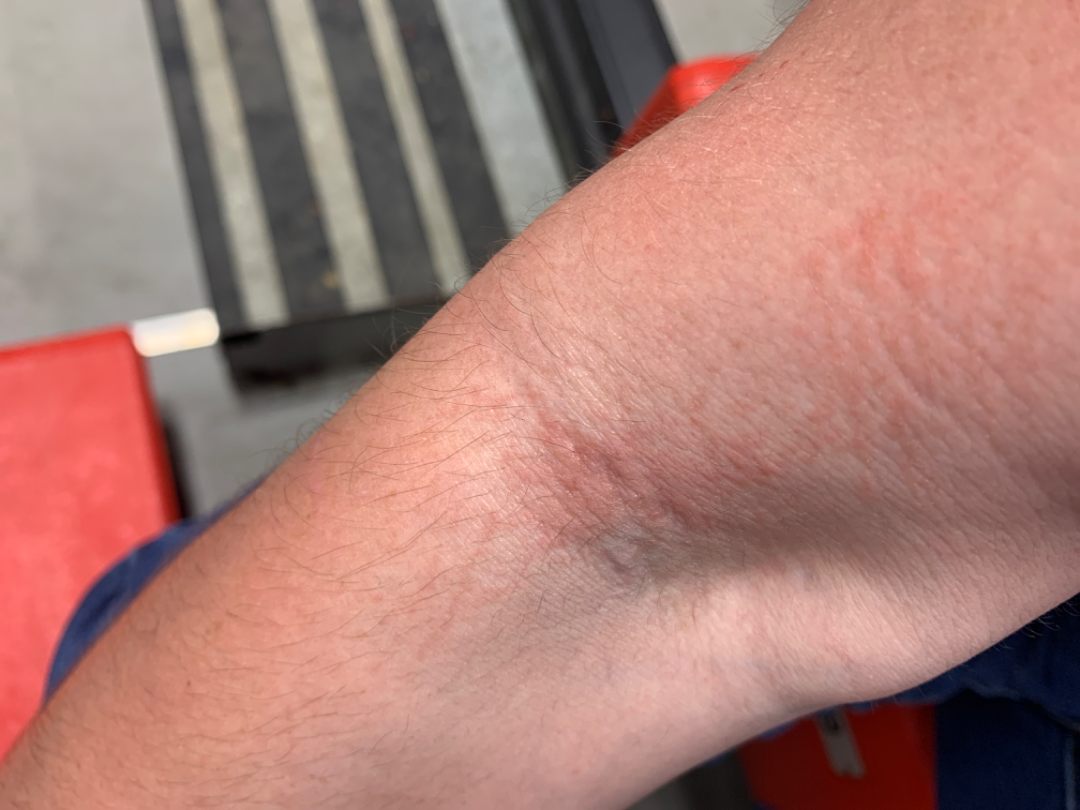assessment=a single dermatologist reviewed the case: most consistent with Eczema